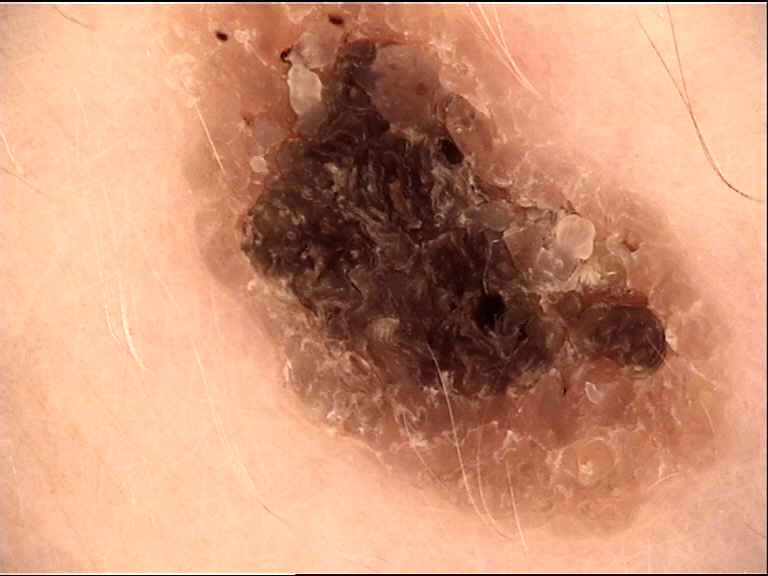image type: dermatoscopy | label: seborrheic keratosis (expert consensus).